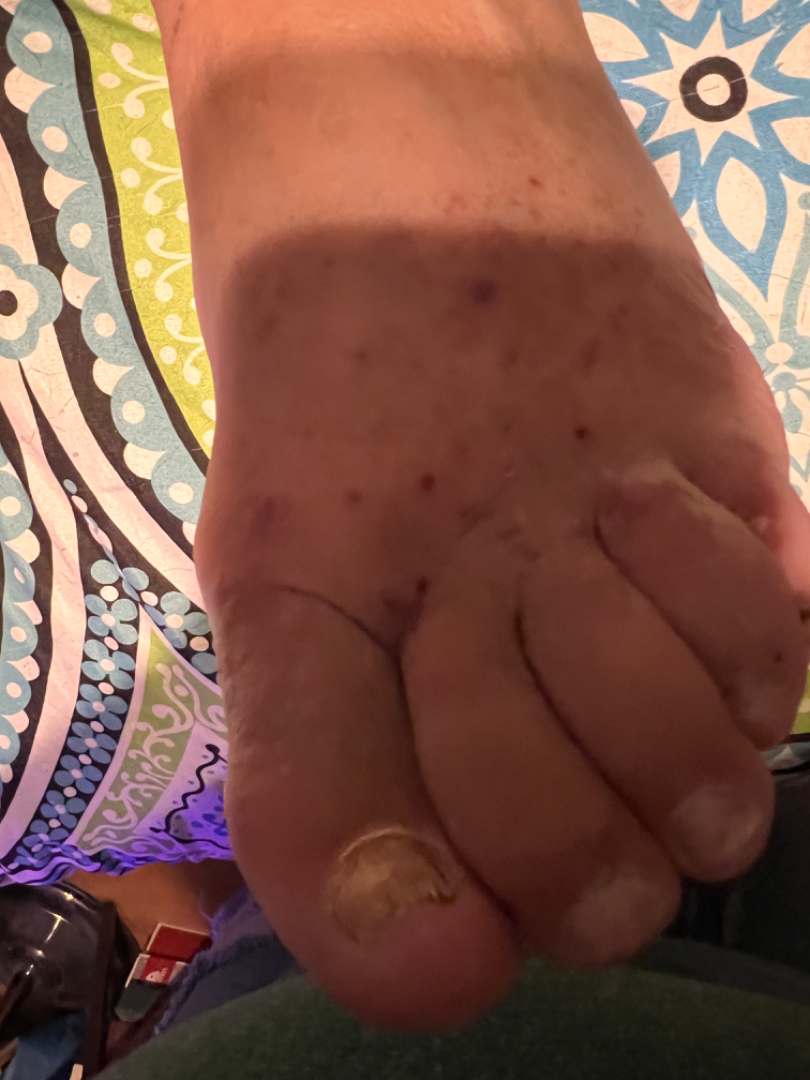The dermatologist could not determine a likely condition from the photograph alone. The photo was captured at a distance. Reported lesion symptoms include burning, bleeding and itching. The patient is 50–59, male. Skin tone: self-reported Fitzpatrick skin type III; human graders estimated Monk Skin Tone 3 or 5.